A dermatoscopic image of a skin lesion:
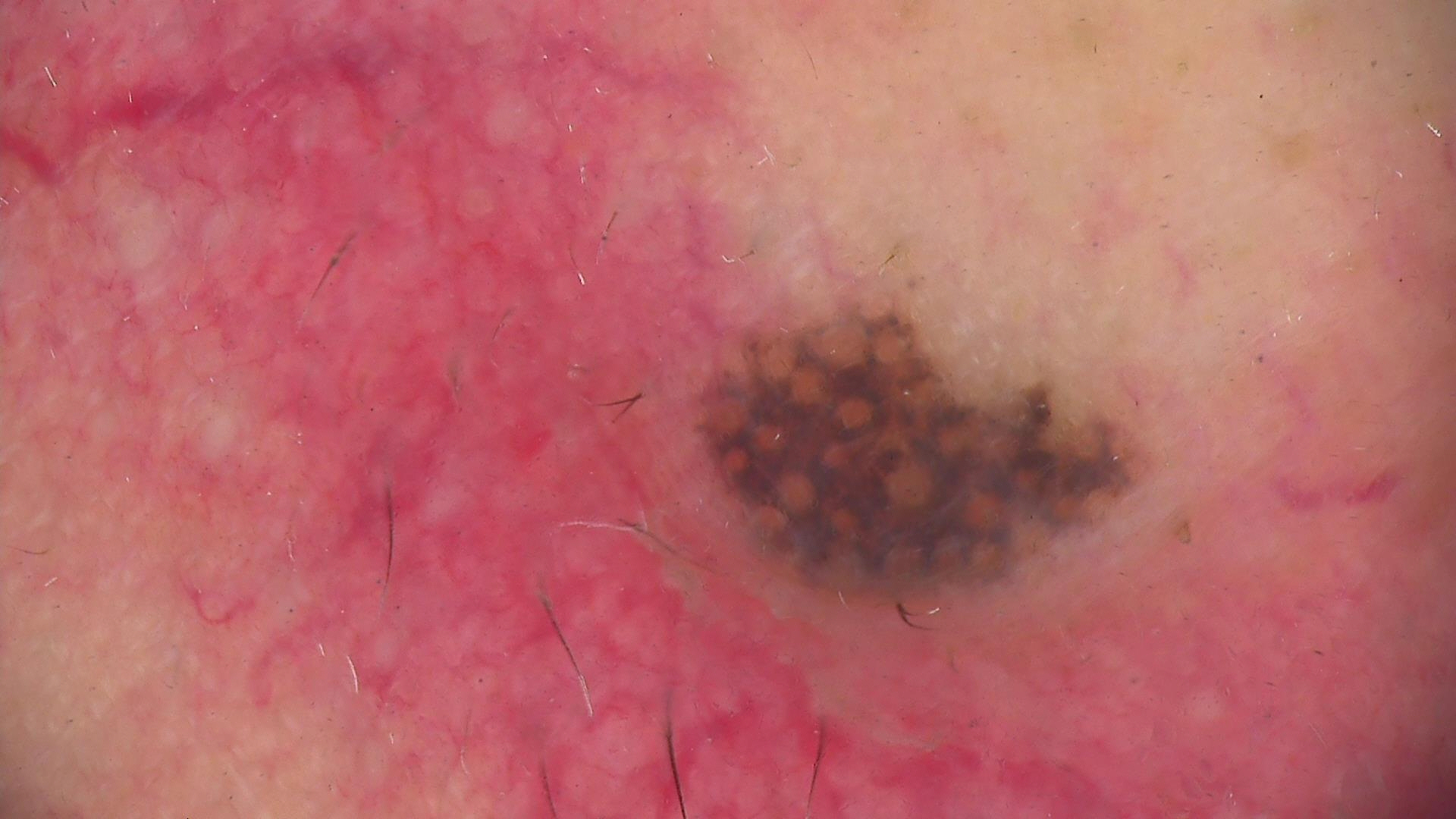<lesion>
  <diagnosis>
    <name>Miescher nevus</name>
    <code>mcb</code>
    <malignancy>benign</malignancy>
    <super_class>melanocytic</super_class>
    <confirmation>expert consensus</confirmation>
  </diagnosis>
</lesion>